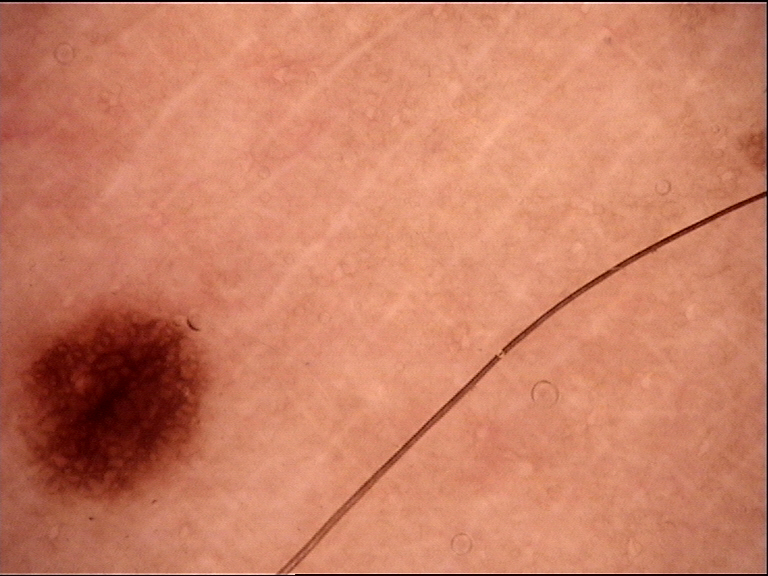- imaging · dermoscopy
- assessment · junctional nevus (expert consensus)